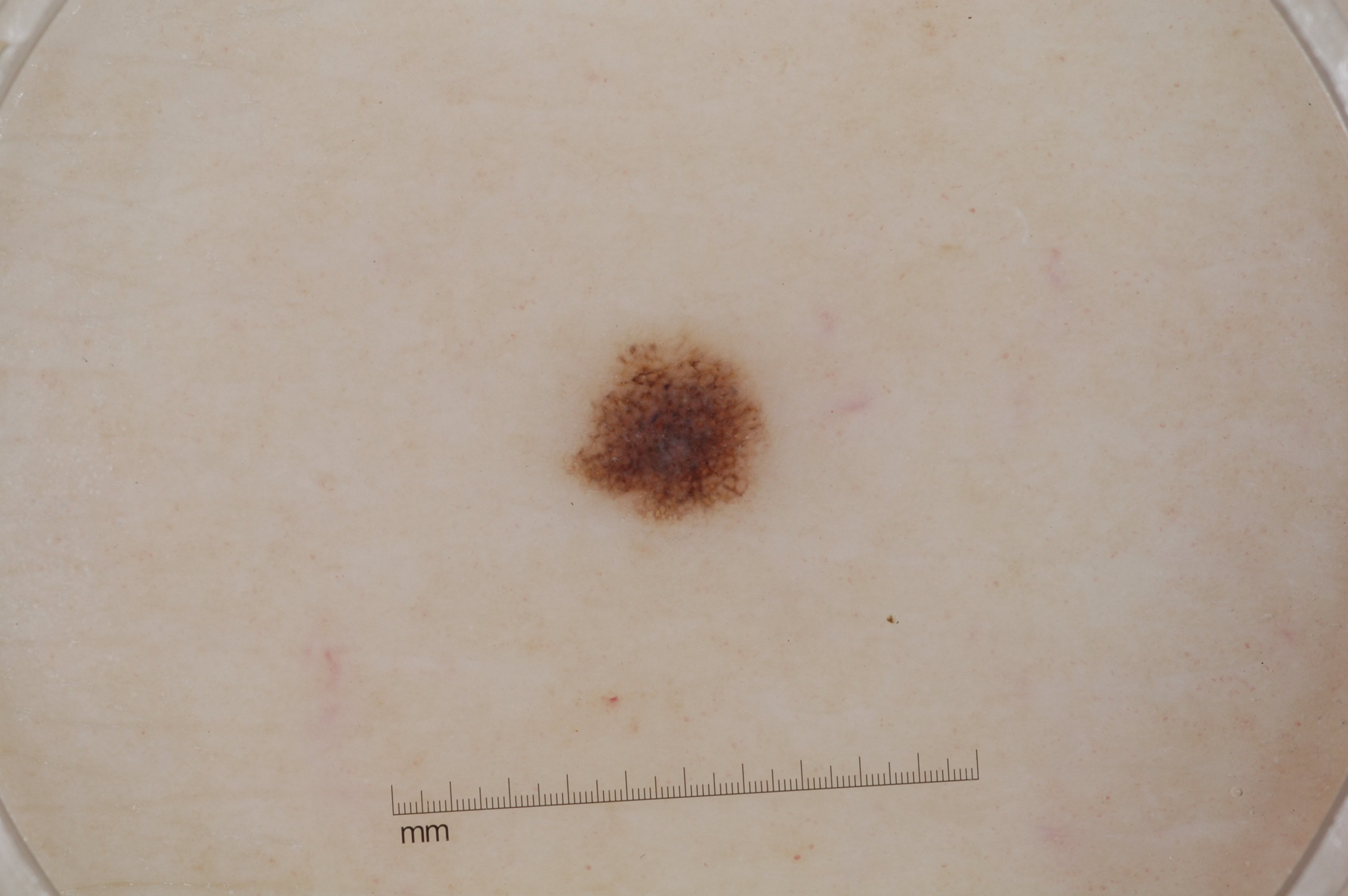Case summary:
– modality · dermoscopic image
– subject · female, approximately 75 years of age
– dermoscopic findings · milia-like cysts and pigment network
– size · ~2% of the field
– lesion location · 569 329 769 525
– diagnostic label · a melanocytic nevus